The lesion involves the arm · the contributor reports itching · no relevant systemic symptoms · texture is reported as raised or bumpy · this image was taken at a distance · the contributor is a male aged 18–29 · present for about one day · the patient considered this a rash — 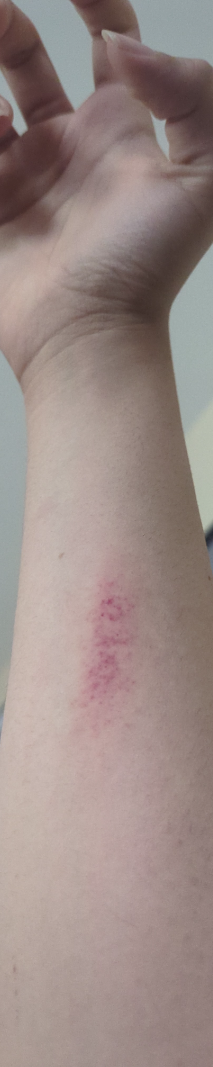The differential, in no particular order, includes Irritant Contact Dermatitis; Abrasion, scrape, or scab; Contact dermatitis; and Eczema; a more distant consideration is Allergic Contact Dermatitis.